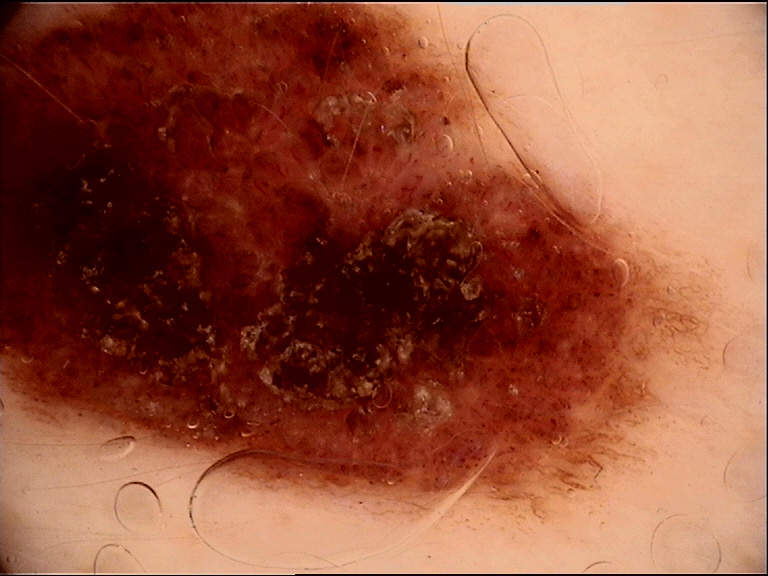| key | value |
|---|---|
| lesion type | banal |
| diagnostic label | congenital compound nevus (expert consensus) |